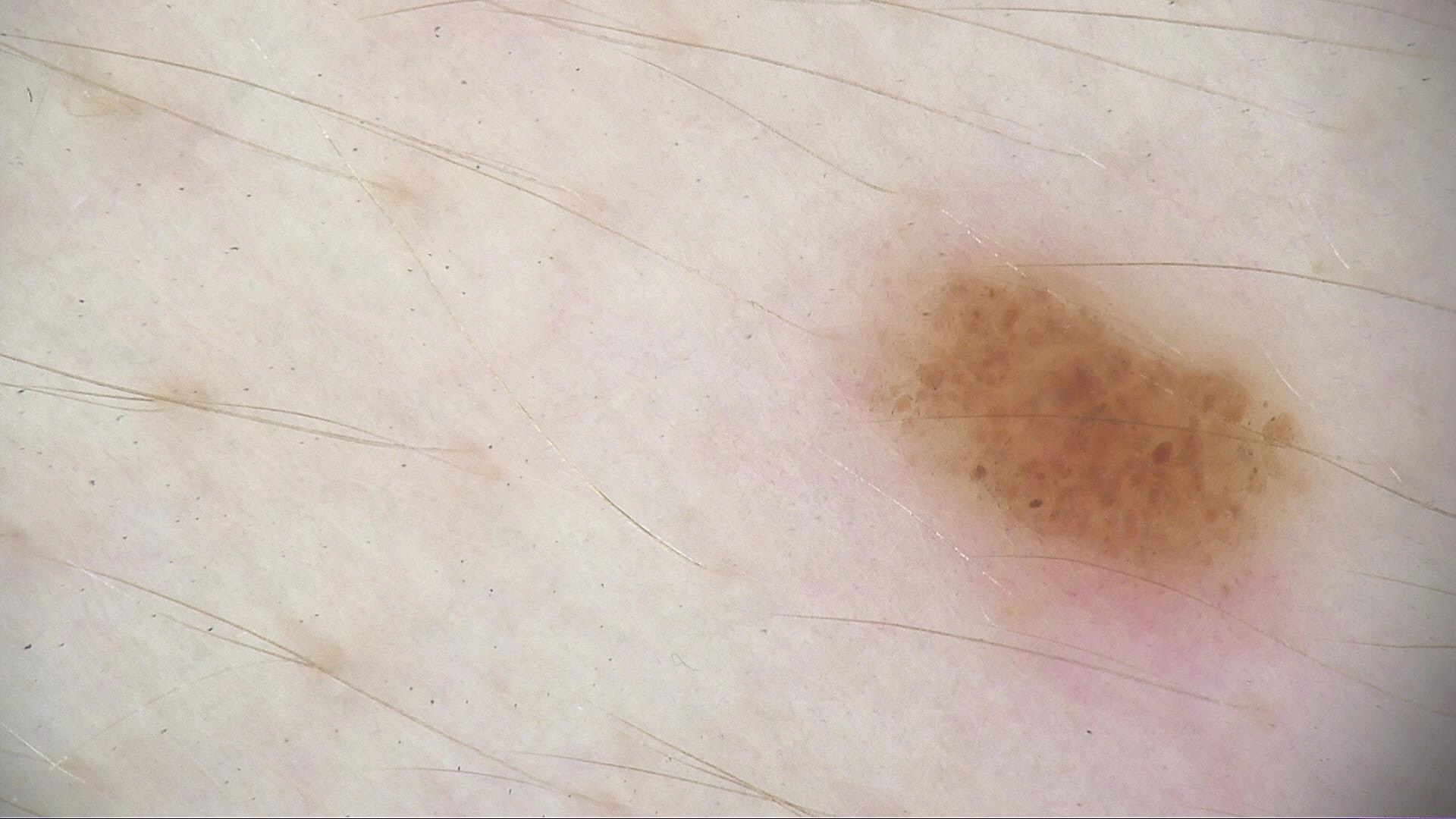image — dermatoscopy
class — junctional nevus (expert consensus)